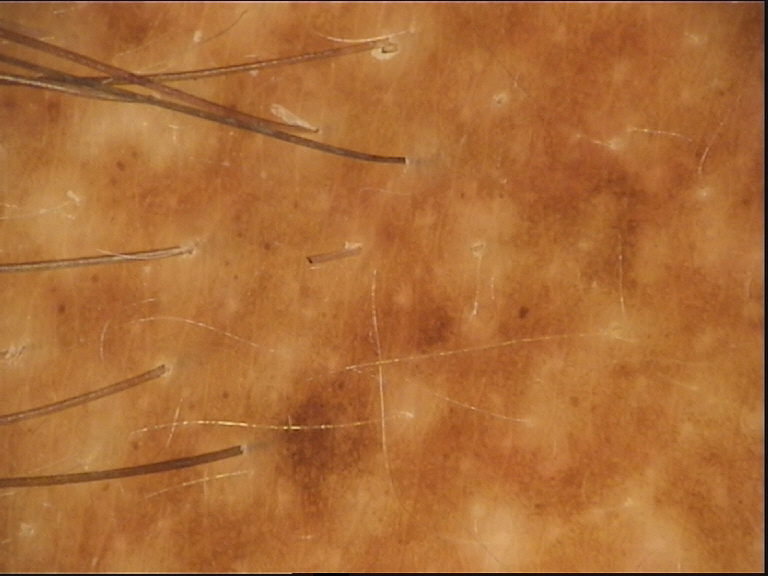Diagnosed as a banal lesion — a congenital compound nevus.